The patient is Fitzpatrick skin type III · a female subject 42 years old: 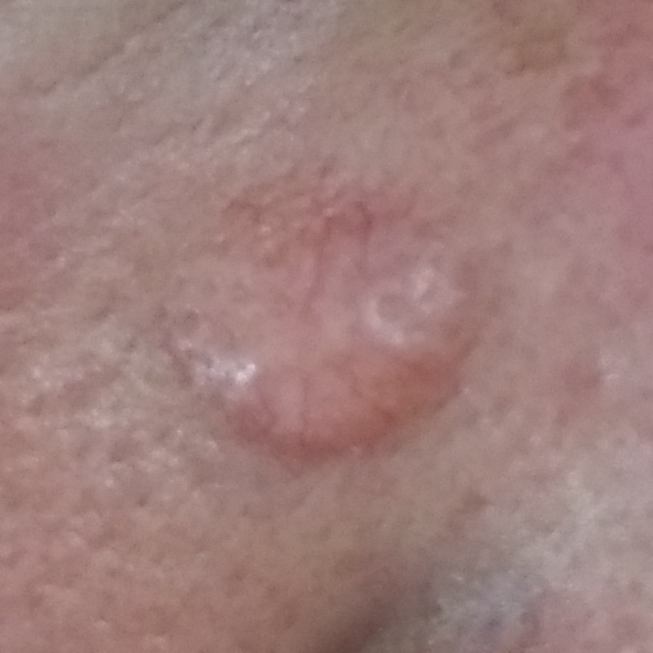Findings: The lesion is located on the nose. The lesion measures approximately 11 × 9 mm. By the patient's account, the lesion has grown, has changed, is elevated, and itches. Conclusion: Histopathologically confirmed as a malignant skin lesion — a basal cell carcinoma.